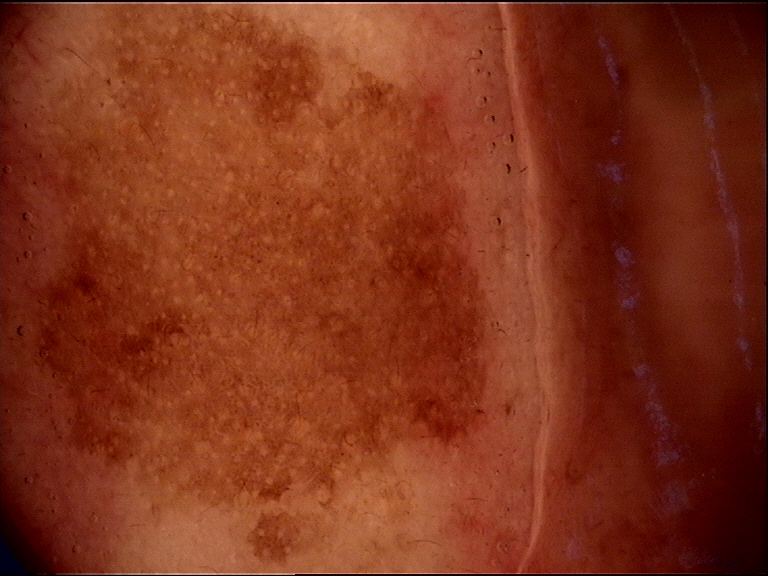Case:
• imaging: dermoscopy
• classification: keratinocytic
• diagnosis: seborrheic keratosis (expert consensus)